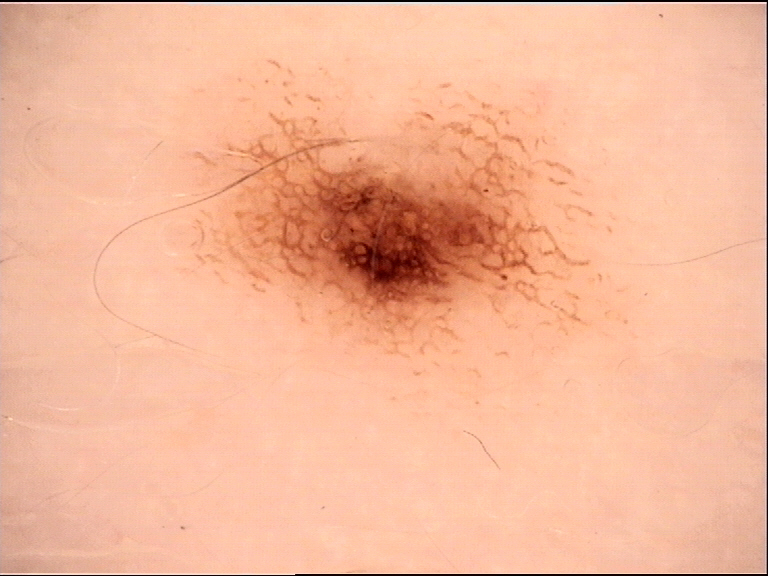Consistent with a benign lesion — a dysplastic junctional nevus.